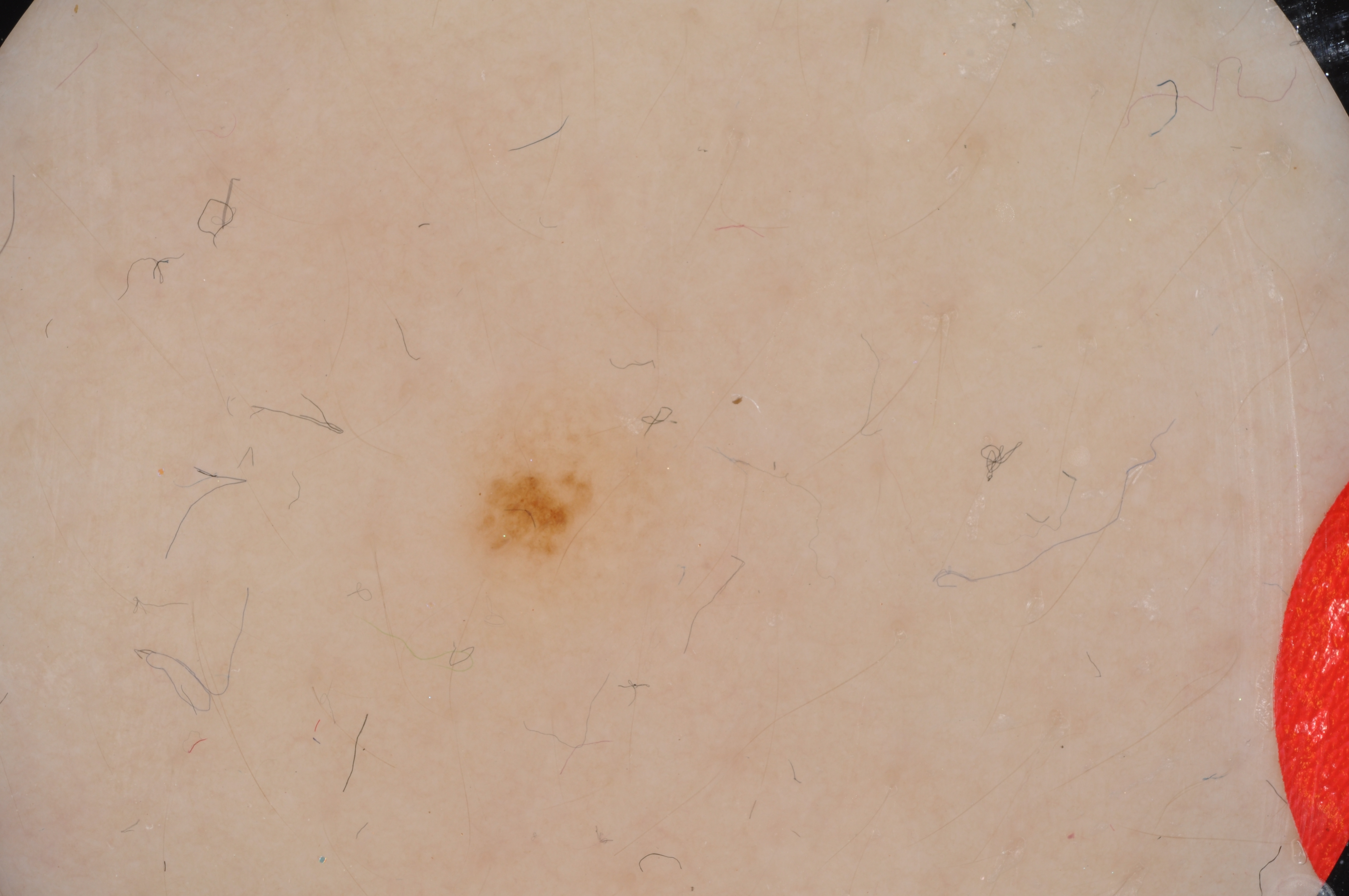Dermoscopy of a skin lesion.
Dermoscopic assessment notes globules, with no streaks, milia-like cysts, pigment network, or negative network.
As (left, top, right, bottom), the lesion spans (455, 386, 678, 605).
The diagnostic assessment was a melanocytic nevus.